Female contributor, age 18–29. The photograph was taken at an angle. The affected area is the back of the hand.
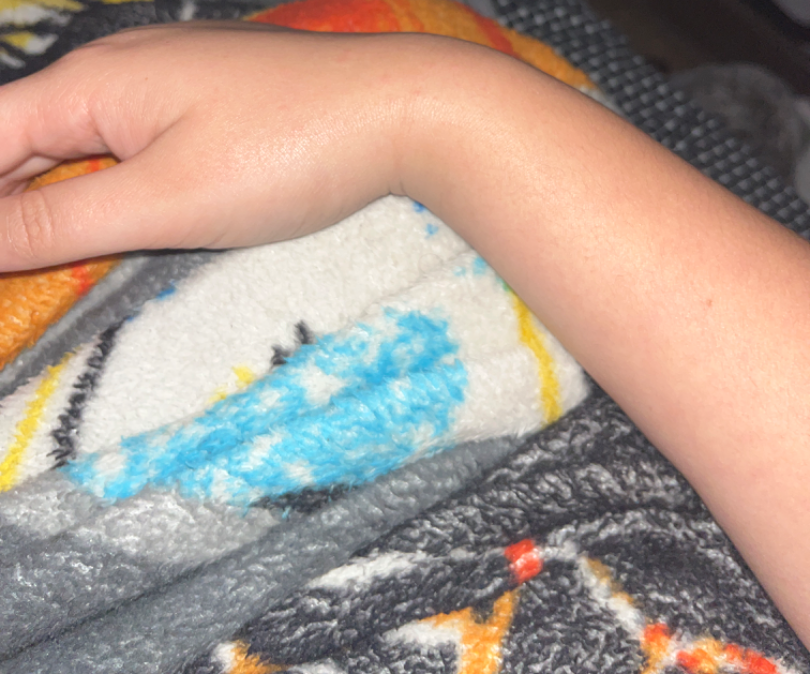assessment — ungradable on photographic review | symptoms — itching | lesion texture — raised or bumpy | skin tone — Fitzpatrick phototype III; non-clinician graders estimated Monk Skin Tone 2 or 3 | patient describes the issue as — a rash | other reported symptoms — none reported.